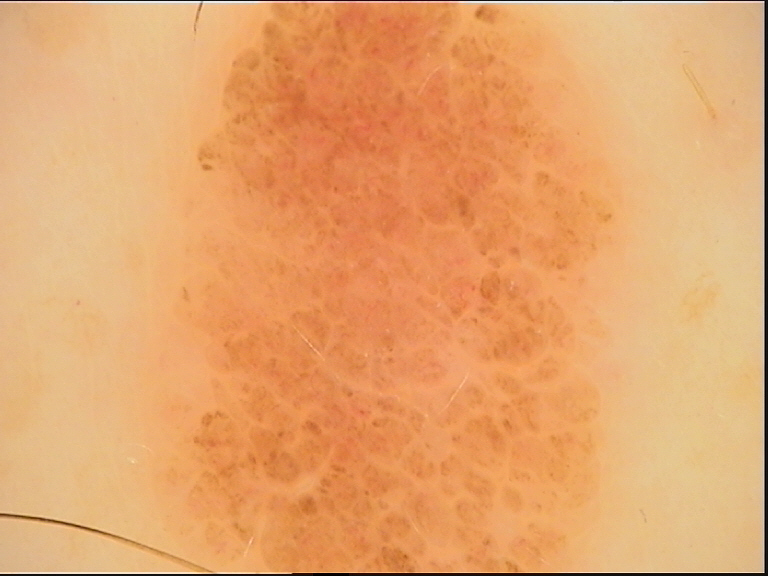Q: What is the imaging modality?
A: dermatoscopy
Q: What is this lesion?
A: compound nevus (expert consensus)